A dermoscopy image of a single skin lesion.
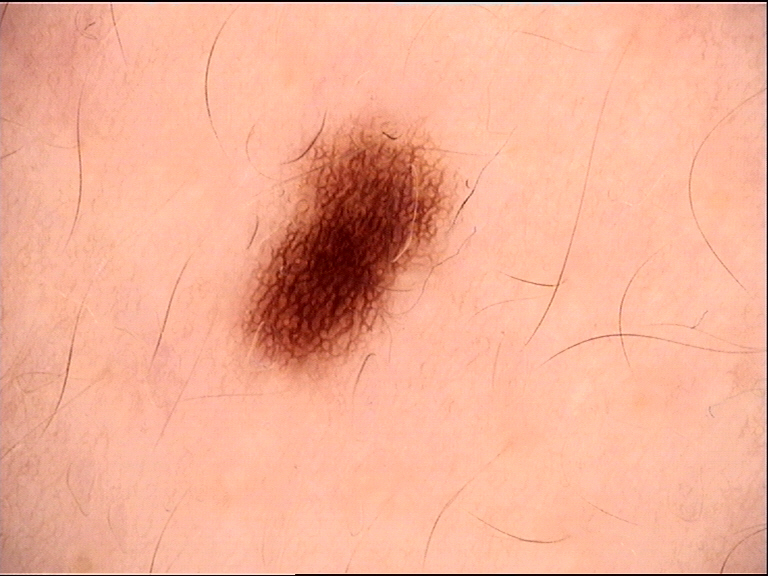Labeled as a dysplastic junctional nevus.